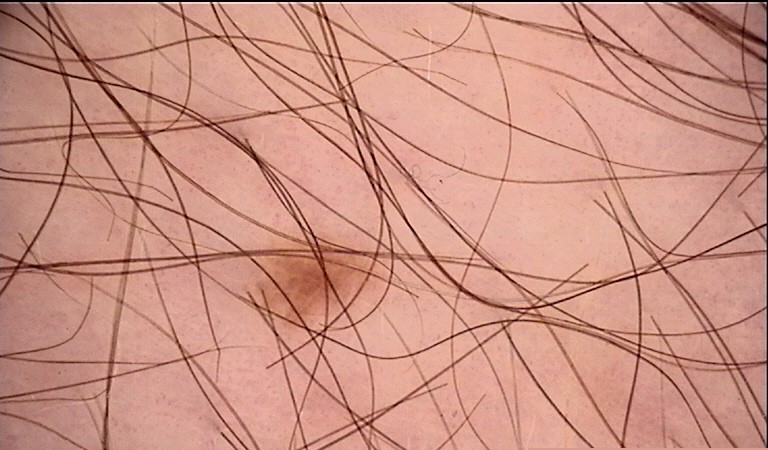| key | value |
|---|---|
| image type | dermatoscopy |
| assessment | junctional nevus (expert consensus) |